A skin lesion imaged with a dermatoscope. A male subject, roughly 55 years of age — 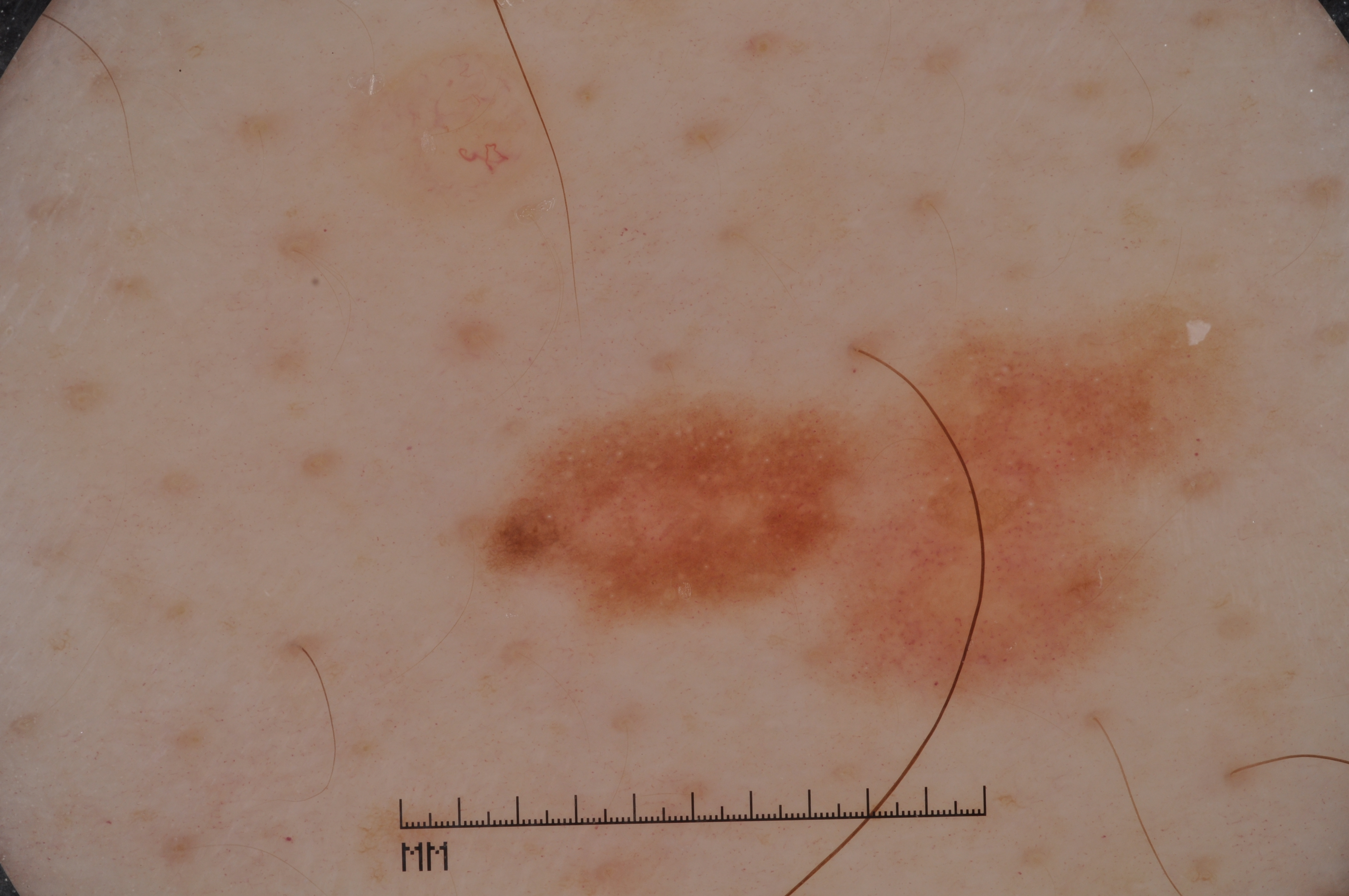{"lesion_location": {"bbox_xyxy": [461, 287, 1254, 709]}, "lesion_extent": {"approx_field_fraction_pct": 20}, "dermoscopic_features": {"present": ["pigment network", "milia-like cysts"], "absent": ["streaks", "negative network"]}, "diagnosis": {"name": "melanoma", "malignancy": "malignant", "lineage": "melanocytic", "provenance": "histopathology"}}